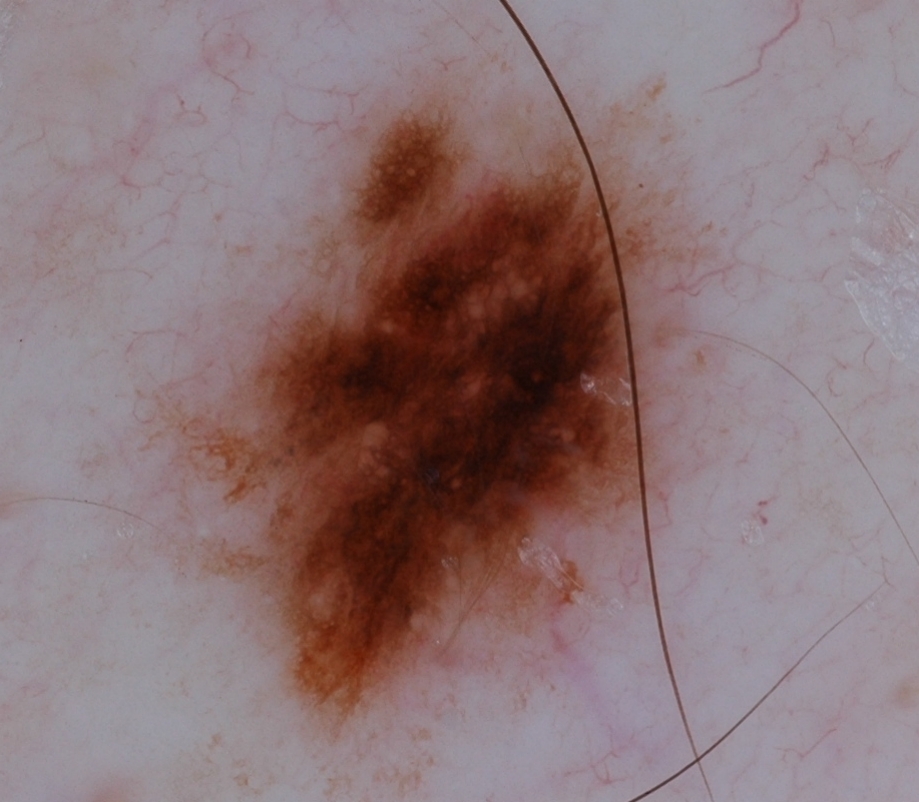A dermatoscopic image of a skin lesion.
As (left, top, right, bottom), the lesion is located at <bbox>125, 50, 757, 797</bbox>.
On dermoscopy, the lesion shows pigment network; no streaks, negative network, milia-like cysts, or globules.
A prominent lesion filling much of the field.
Expert review diagnosed this as a melanocytic nevus, a benign lesion.